Dermoscopy of a skin lesion · a female patient, in their mid-40s: 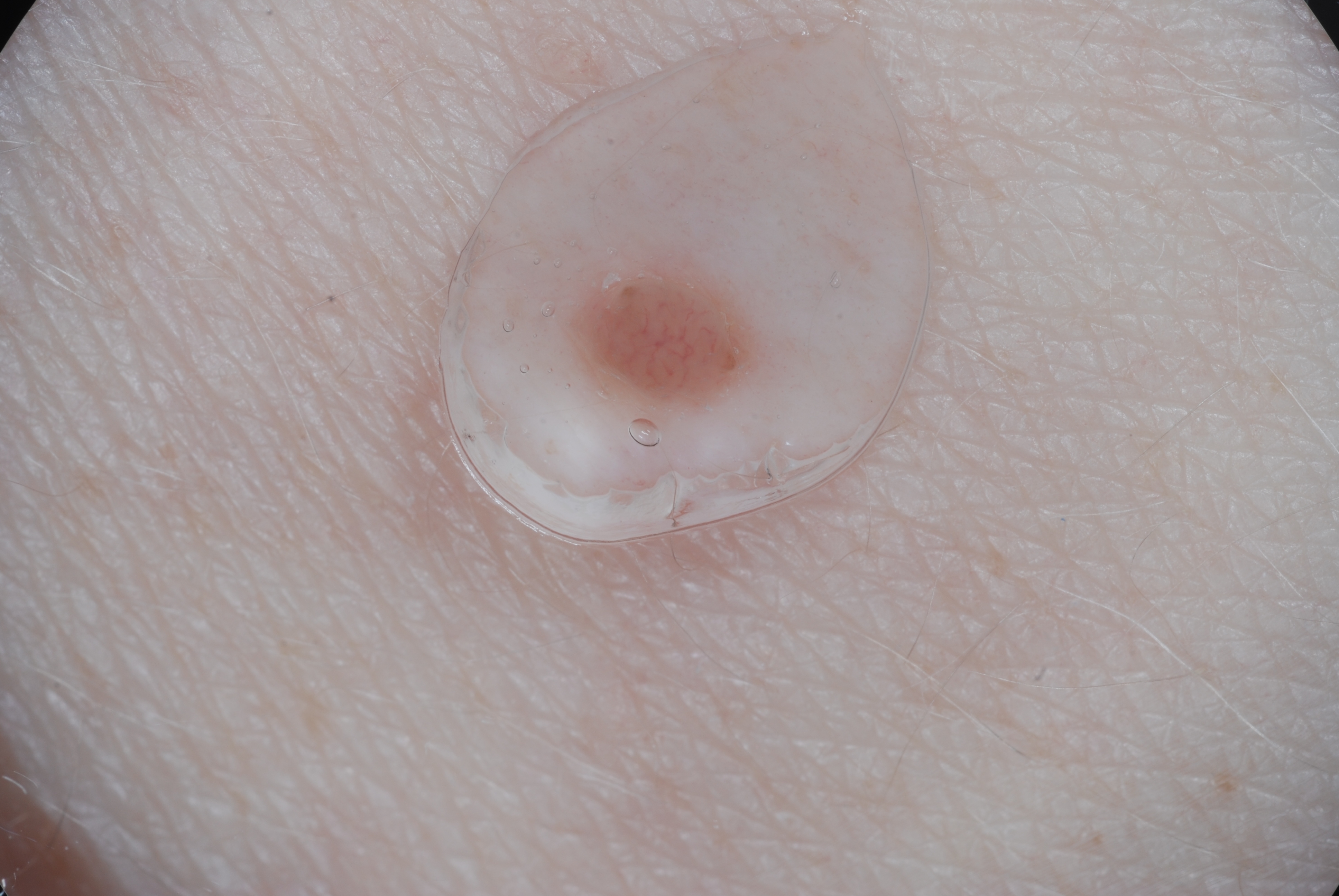As (left, top, right, bottom), the lesion is bounded by bbox=[559, 238, 770, 430].
Dermoscopic assessment notes no negative network, streaks, milia-like cysts, or pigment network.
The lesion takes up about 2% of the image.
Expert review diagnosed this as a melanocytic nevus.